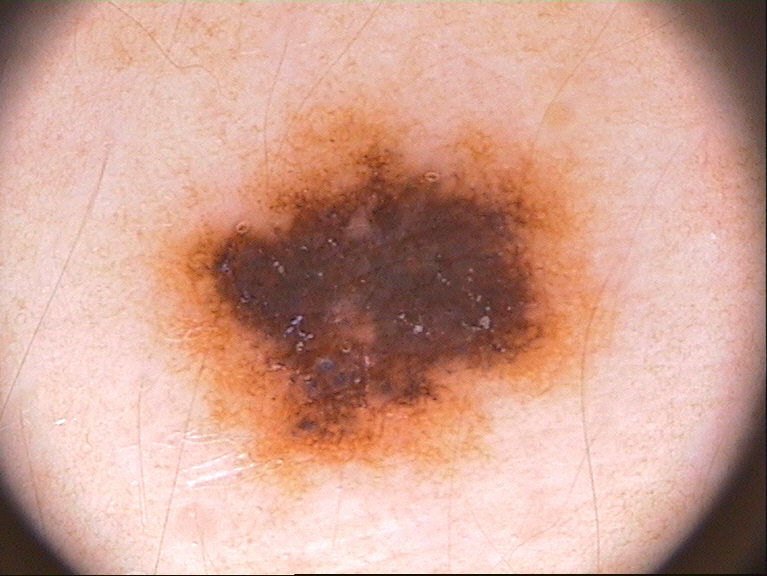subject: male, about 15 years old; image: dermatoscopic image of a skin lesion; lesion size: ~36% of the field; lesion location: box(144, 90, 637, 500); dermoscopic pattern: pigment network and globules; diagnostic label: a melanocytic nevus, a benign skin lesion.